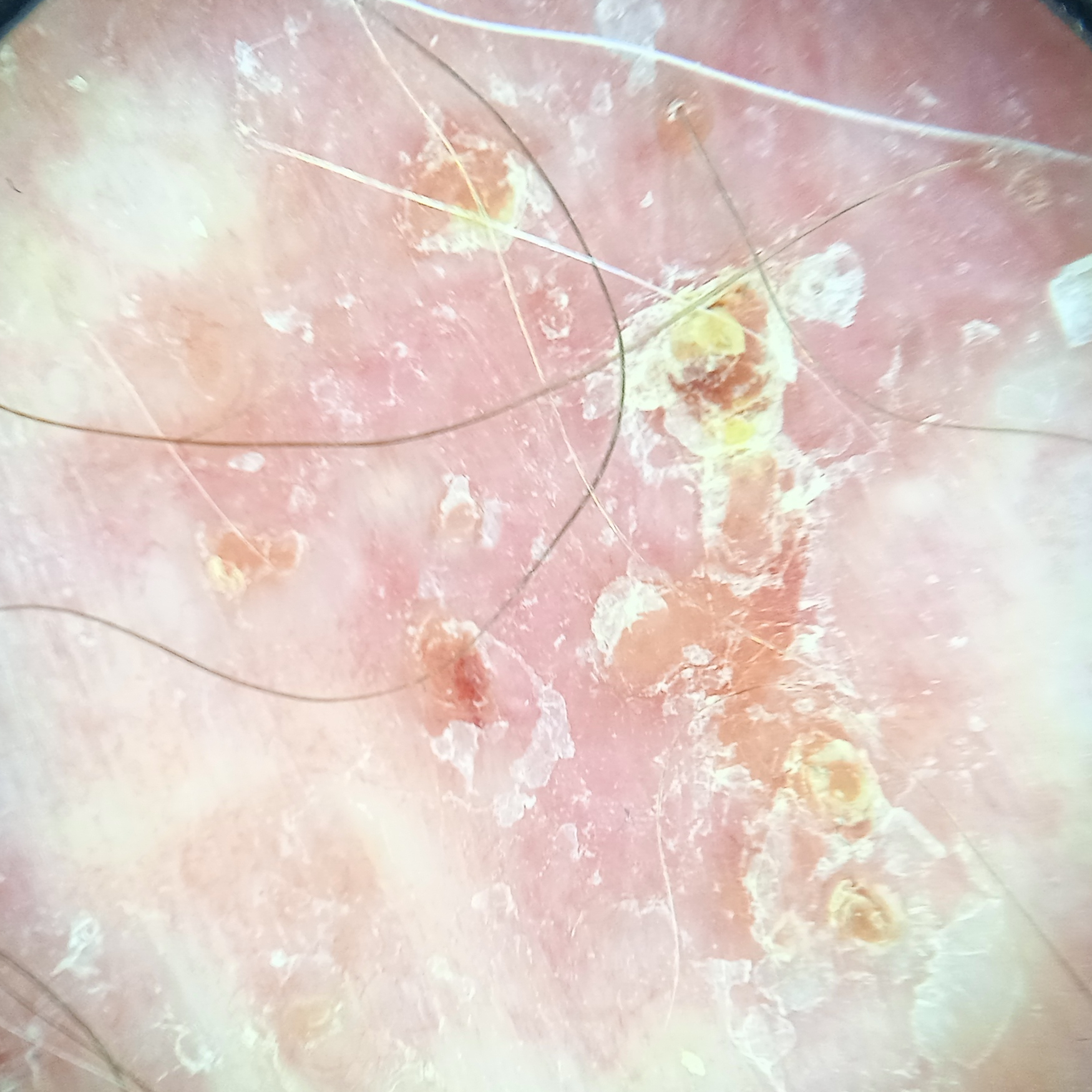The patient says their skin tans without first burning. Referred for assessment of suspected basal cell carcinoma. A dermoscopy image of a skin lesion. The patient reports a personal history of skin cancer. Histopathologically confirmed as a basal cell carcinoma, following a punch biopsy, with a measured thickness of 0.8 mm.